A dermoscopic view of a skin lesion: 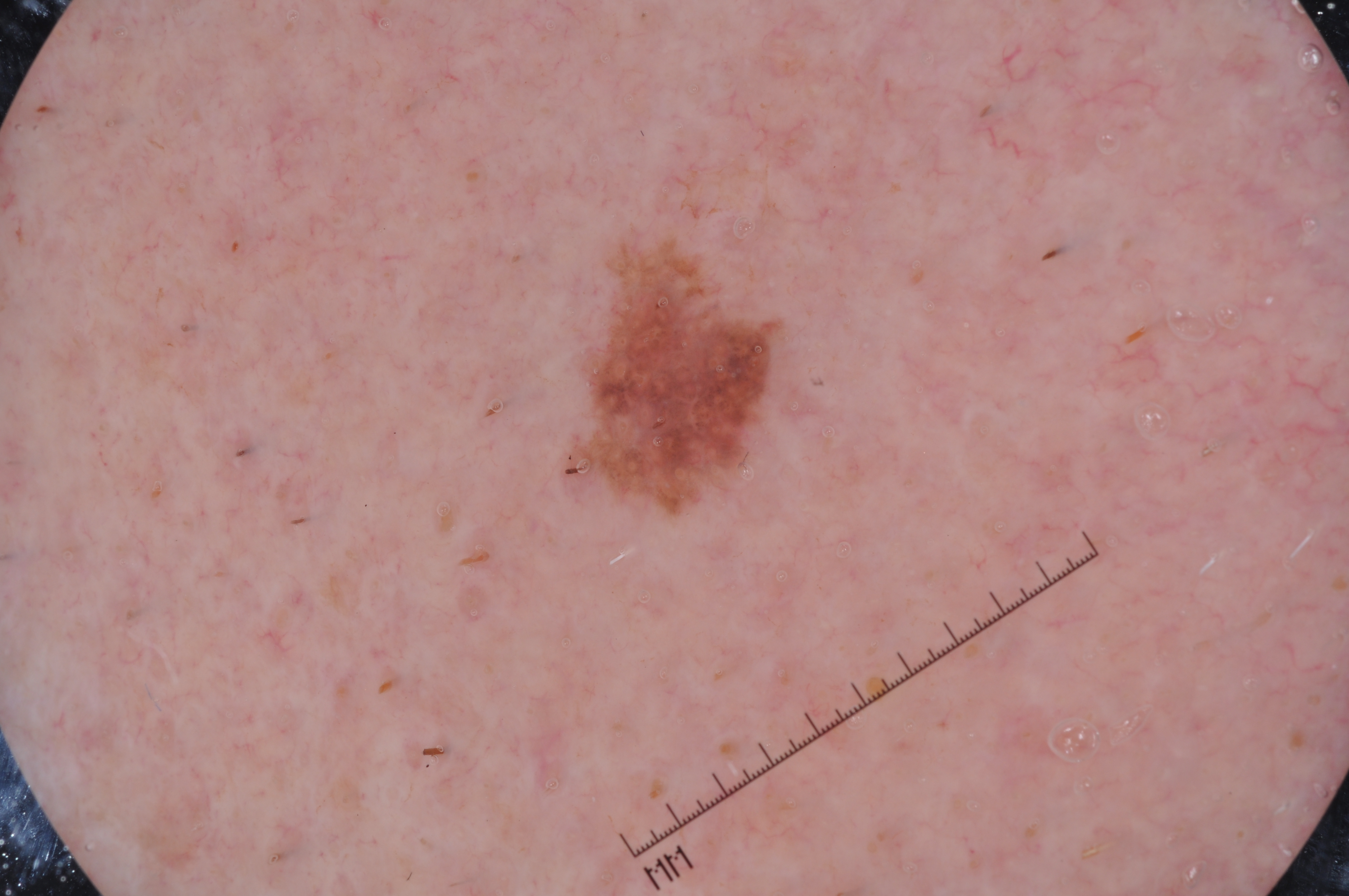  lesion_extent: small
  lesion_location:
    bbox_xyxy:
      - 590
      - 259
      - 780
      - 504
  dermoscopic_features:
    present:
      - negative network
    absent:
      - pigment network
      - streaks
      - milia-like cysts
  diagnosis:
    name: melanoma
    malignancy: malignant
    lineage: melanocytic
    provenance: histopathology